A dermoscopic image of a skin lesion.
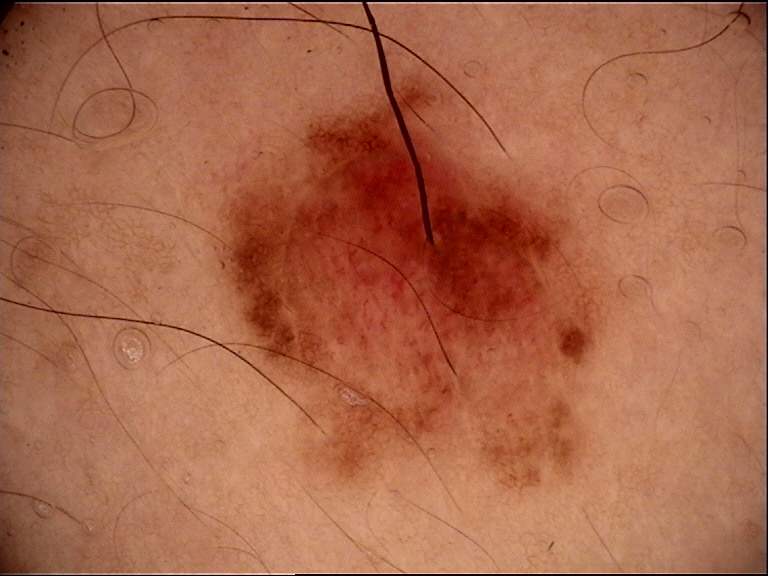diagnosis:
  name: dysplastic compound nevus
  code: cd
  malignancy: benign
  super_class: melanocytic
  confirmation: expert consensus